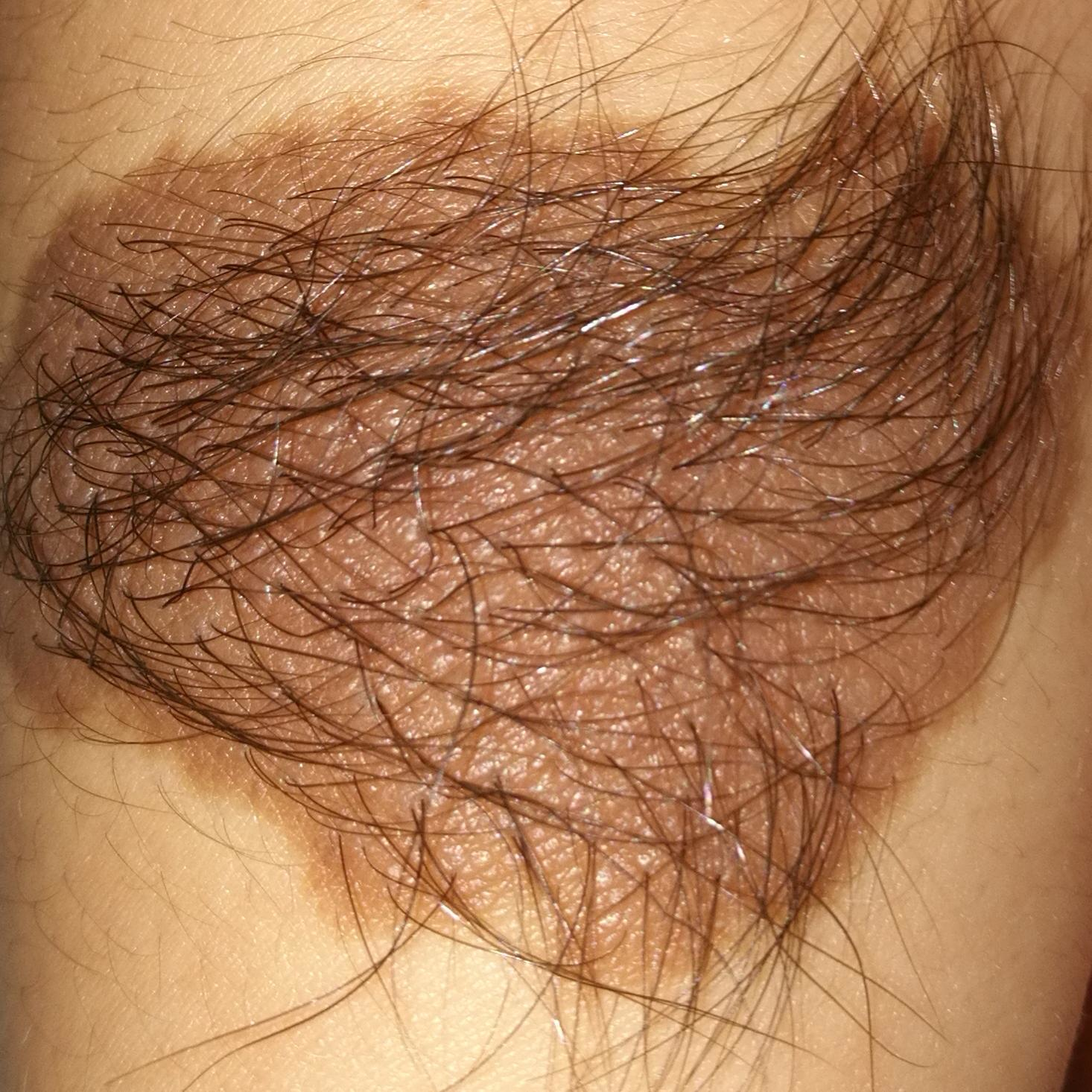Impression: The consensus clinical diagnosis was a nevus.